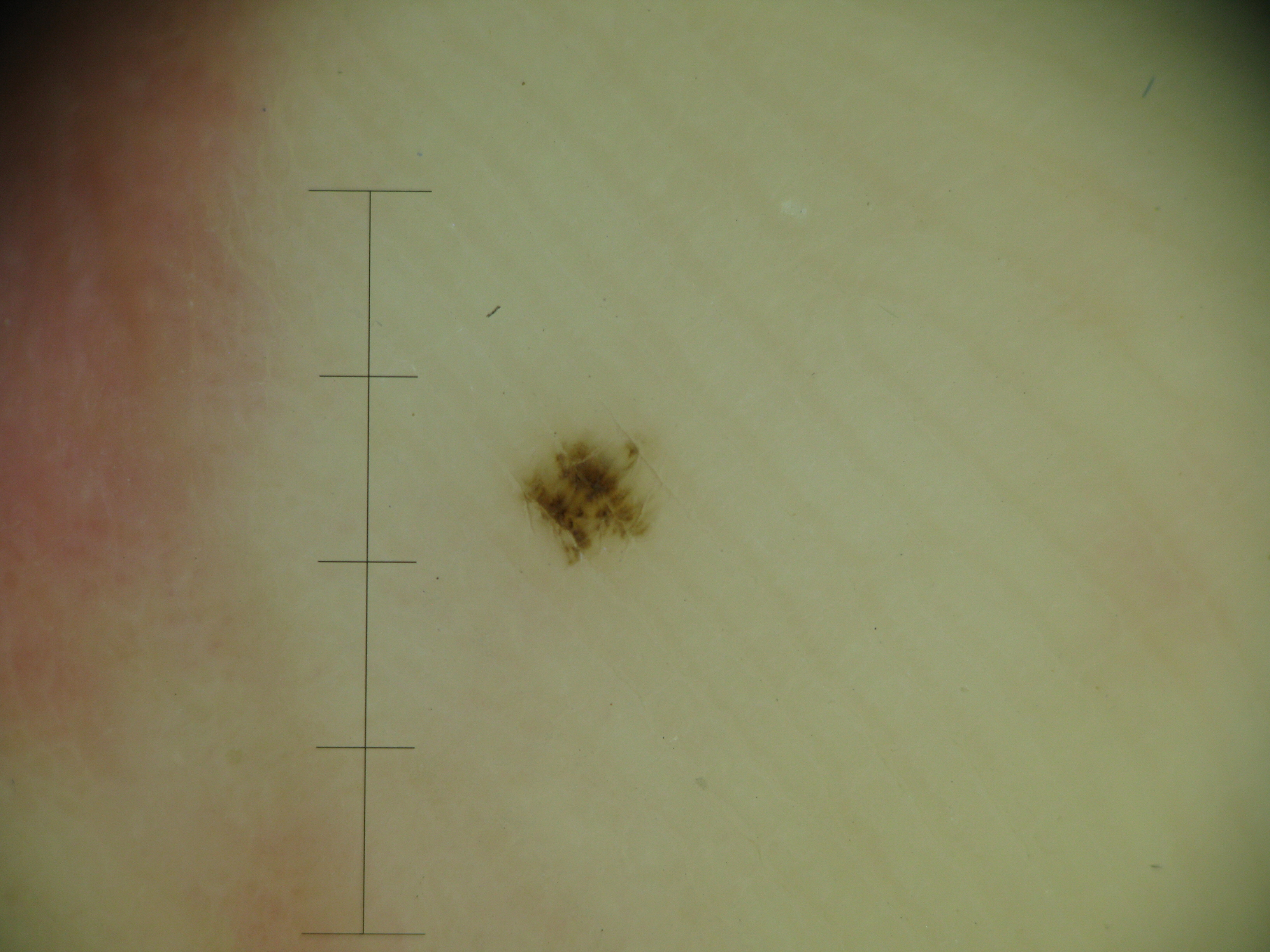Consistent with an acral dysplastic junctional nevus.